Dermoscopy of a skin lesion: 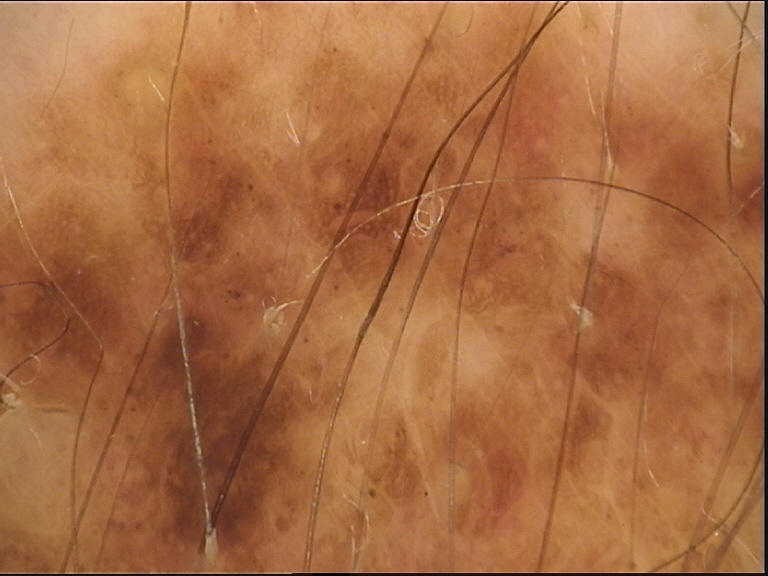This is a banal lesion. Consistent with a congenital compound nevus.